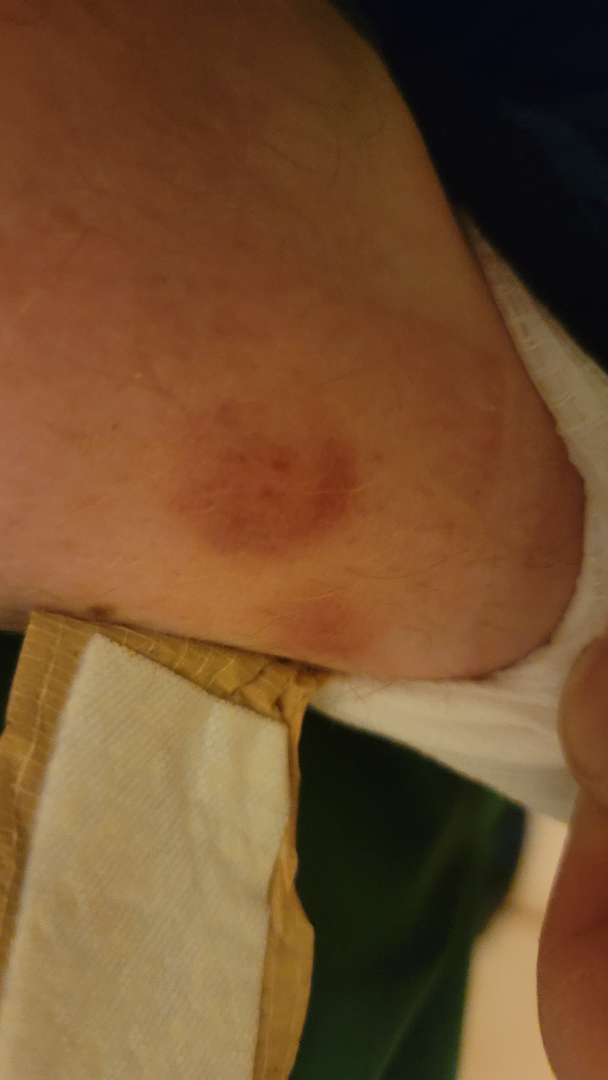* photo taken: at an angle
* contributor: male, age 30–39
* affected area: back of the torso
* clinical impression: most consistent with ecchymoses; also consider Insect Bite; lower on the differential is Pigmented purpuric eruption; less probable is Allergic Contact Dermatitis